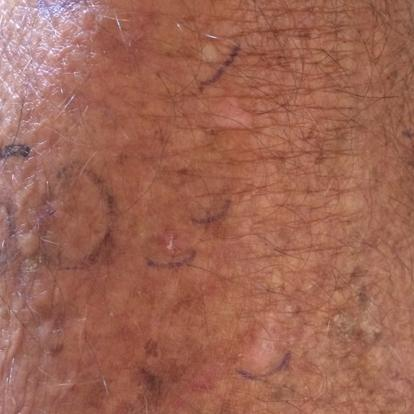{
  "lesion_location": "a forearm",
  "diagnosis": {
    "name": "actinic keratosis",
    "code": "ACK",
    "malignancy": "indeterminate",
    "confirmation": "clinical consensus"
  }
}